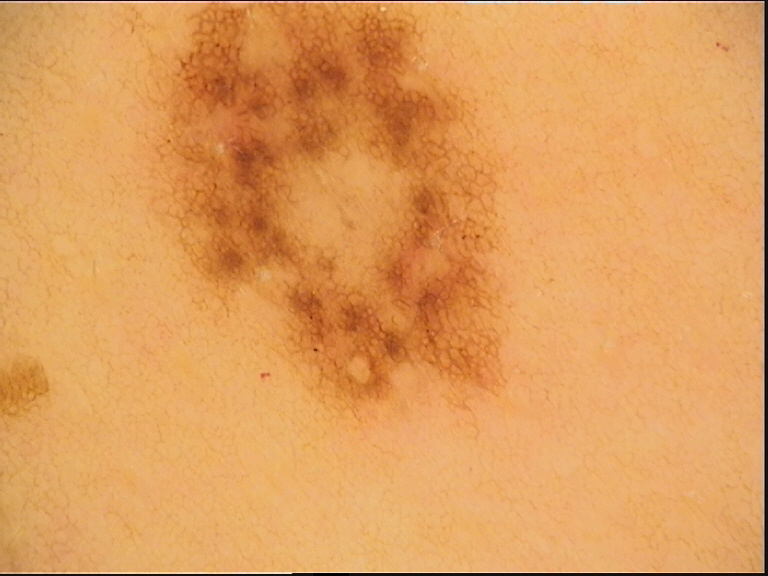A dermoscopic photograph of a skin lesion. The diagnostic label was a dysplastic junctional nevus.